A skin lesion imaged with a dermatoscope, a male subject aged 63 to 67: 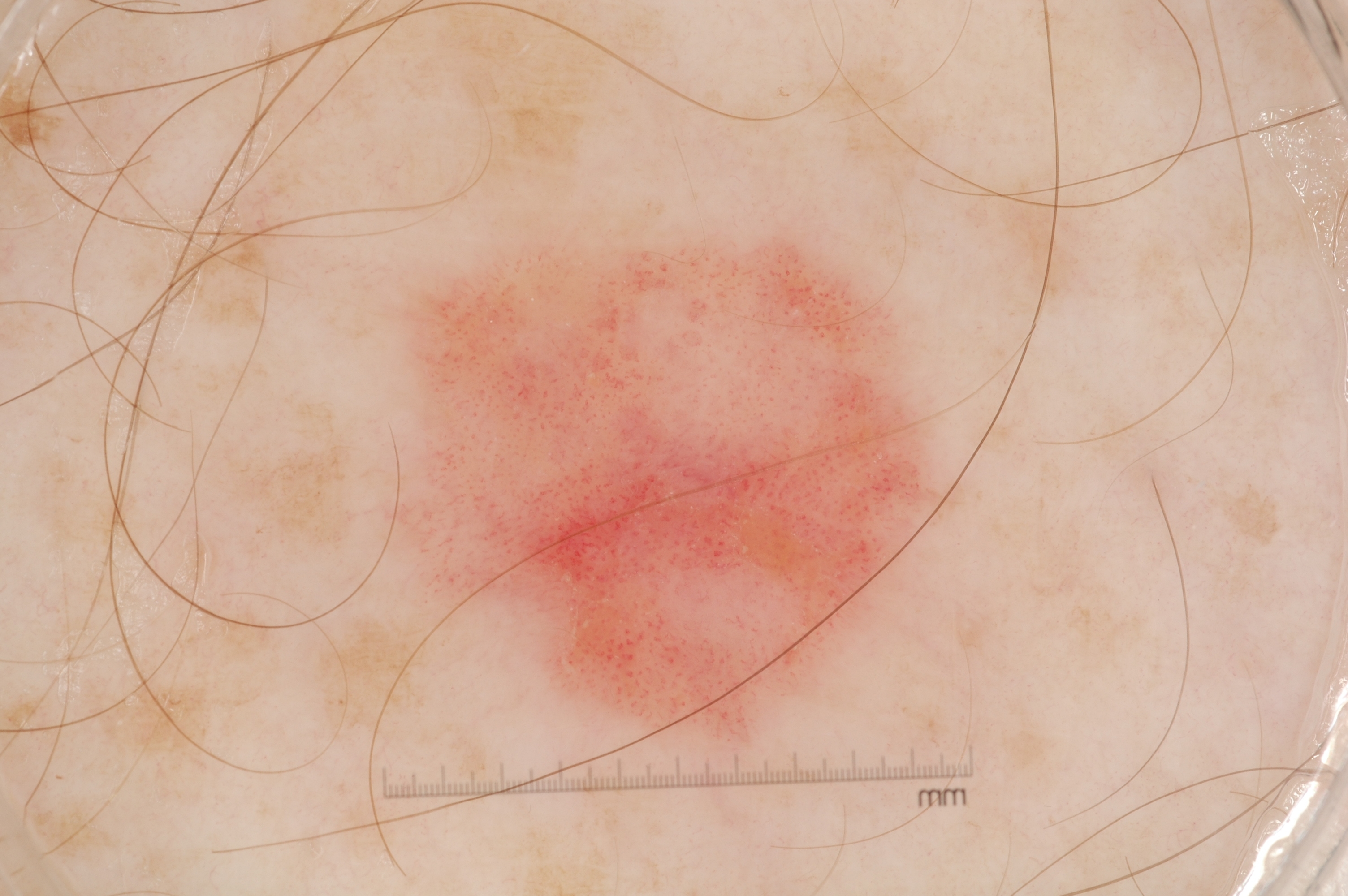Dermoscopically, the lesion shows no pigment network, milia-like cysts, streaks, or negative network. With coordinates (x1, y1, x2, y2), lesion location: <bbox>401, 231, 948, 742</bbox>. Clinically diagnosed as a seborrheic keratosis, a benign skin lesion.